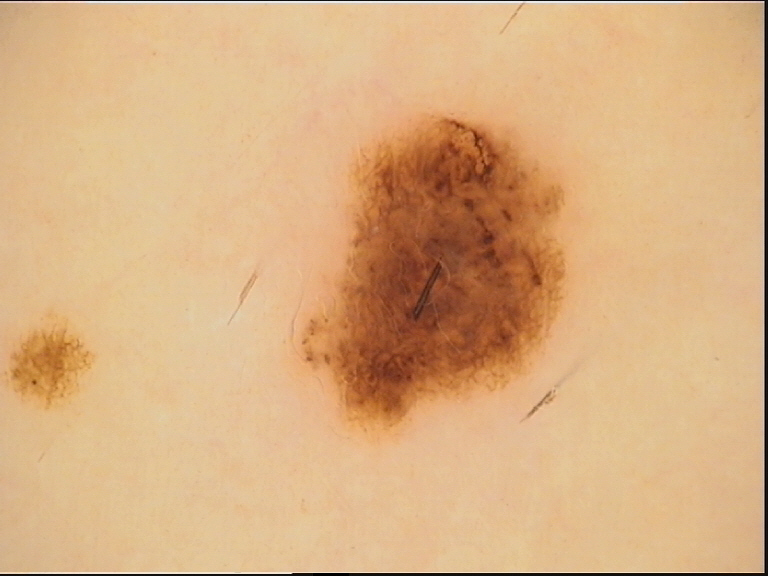Case: Dermoscopy of a skin lesion. Conclusion: The diagnostic label was a dysplastic junctional nevus.